Skin type III · a clinical overview photograph of a skin lesion:
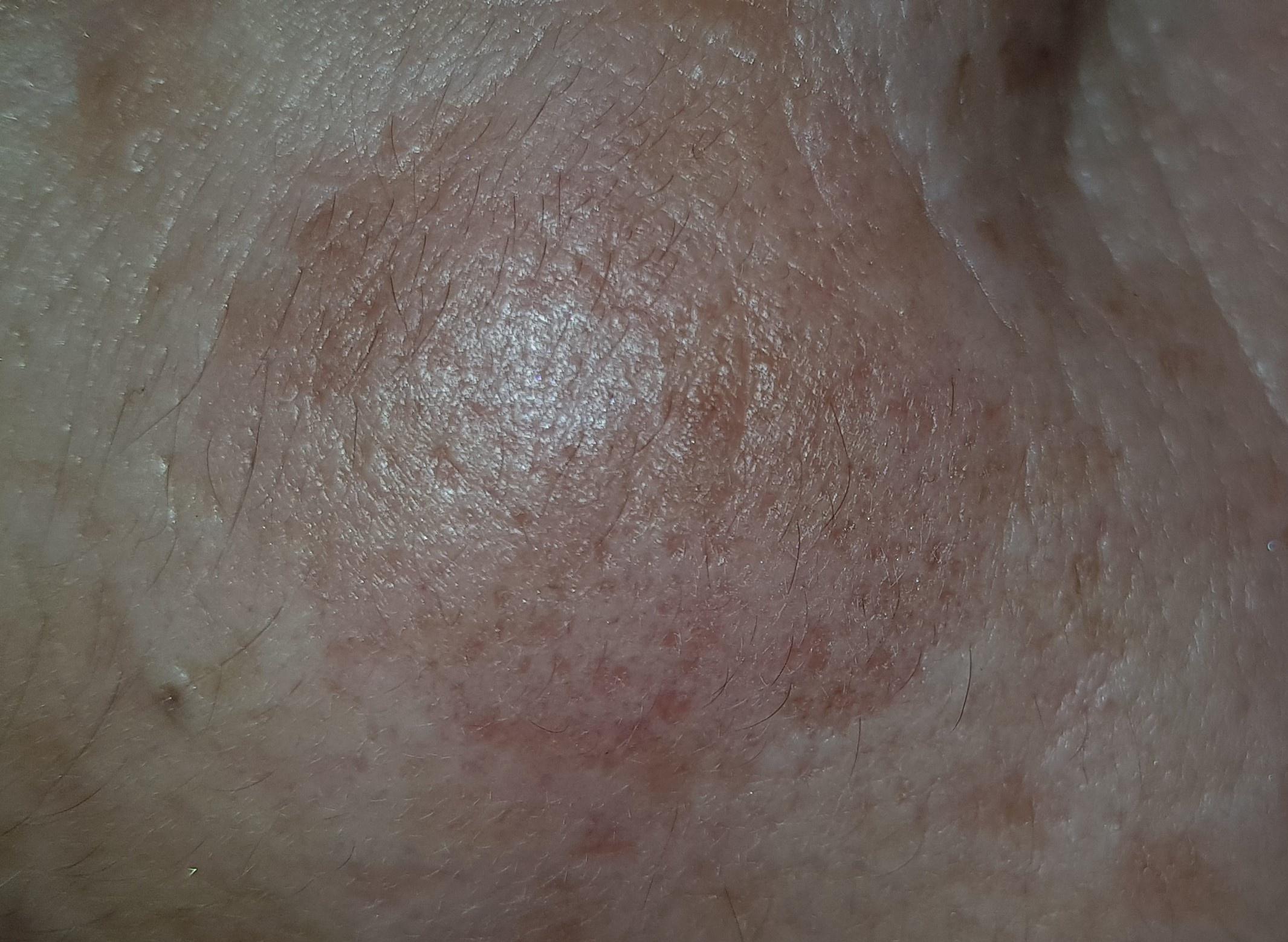On biopsy, the diagnosis was an epidermal lesion — a solar or actinic keratosis.